A female subject aged approximately 65 · a skin lesion imaged with a dermatoscope — 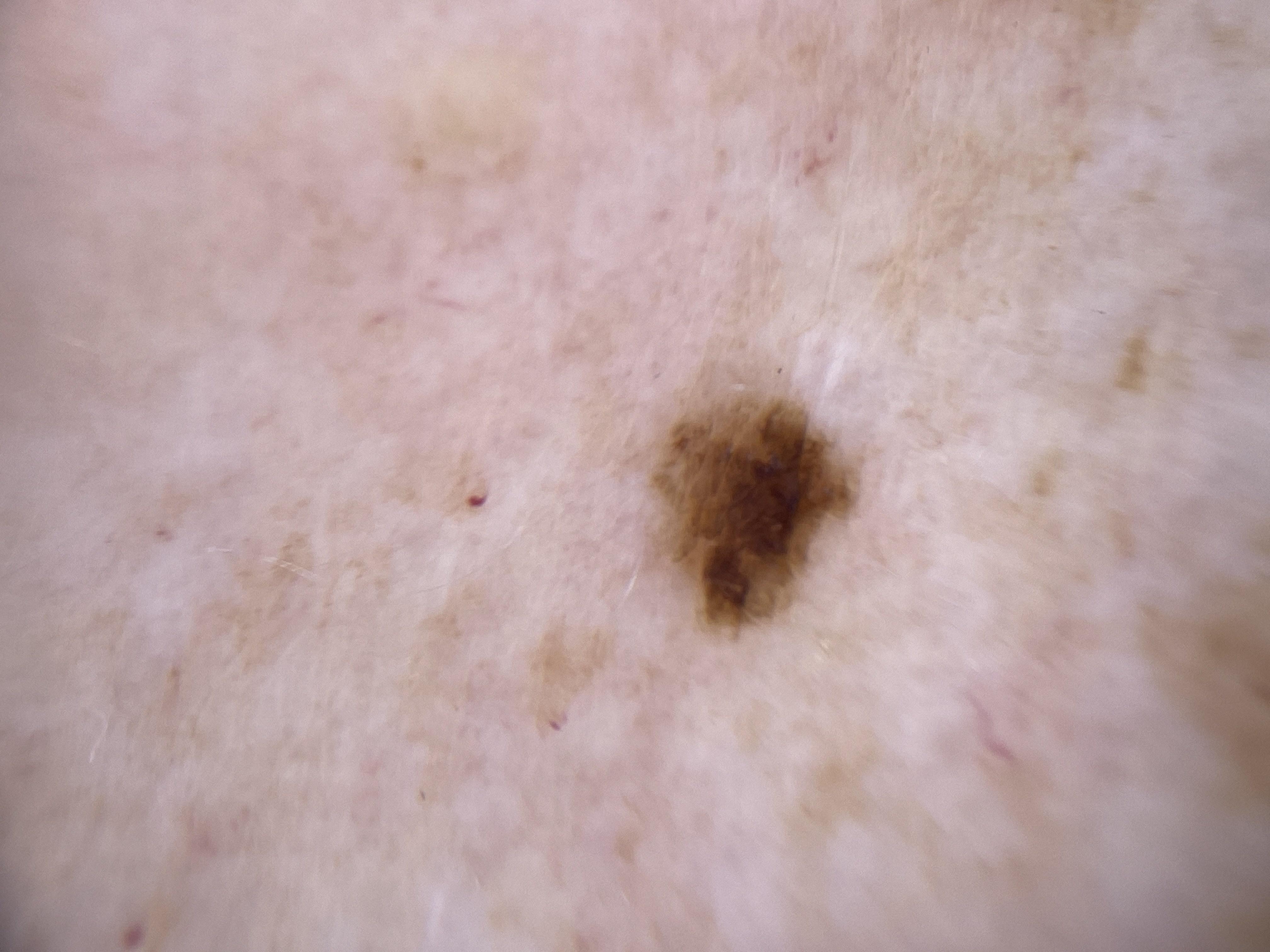The lesion was found on an upper extremity.
The diagnostic impression was a nevus.